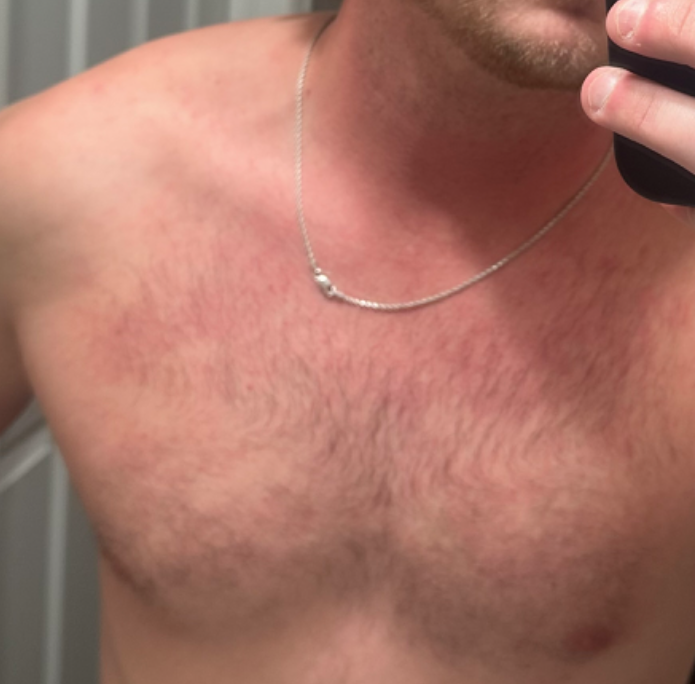Q: Could the case be diagnosed?
A: indeterminate from the photograph
Q: Image view?
A: at an angle
Q: Where on the body?
A: arm, front of the torso and head or neck
Q: Who is the patient?
A: male, age 18–29